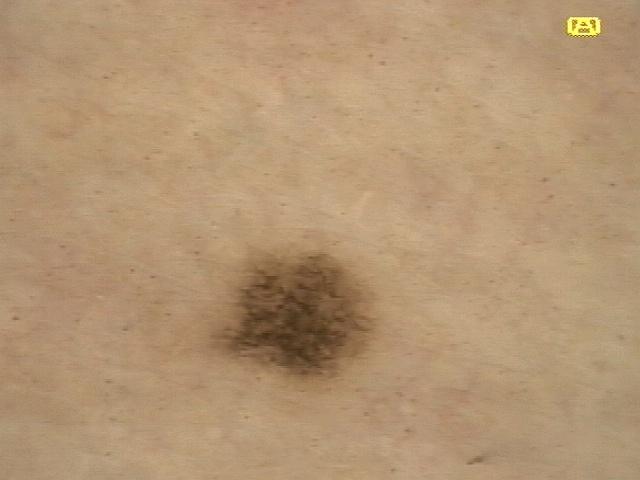image: contact-polarized dermoscopy
subject: female, about 30 years old
body site: the posterior trunk
diagnostic label: Nevus (clinical impression)